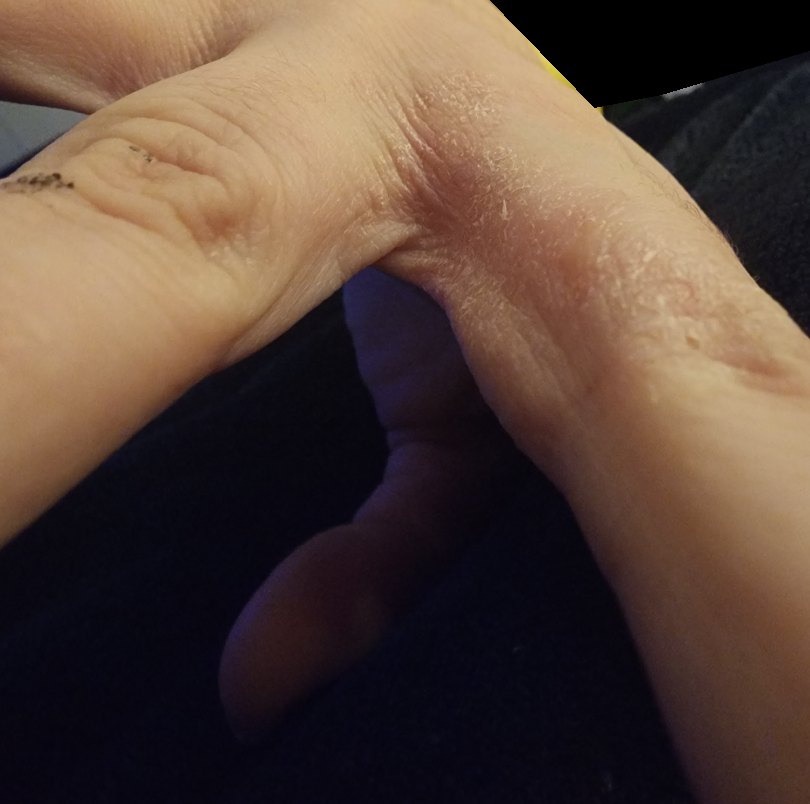On photographic review by a dermatologist: favoring Eczema.